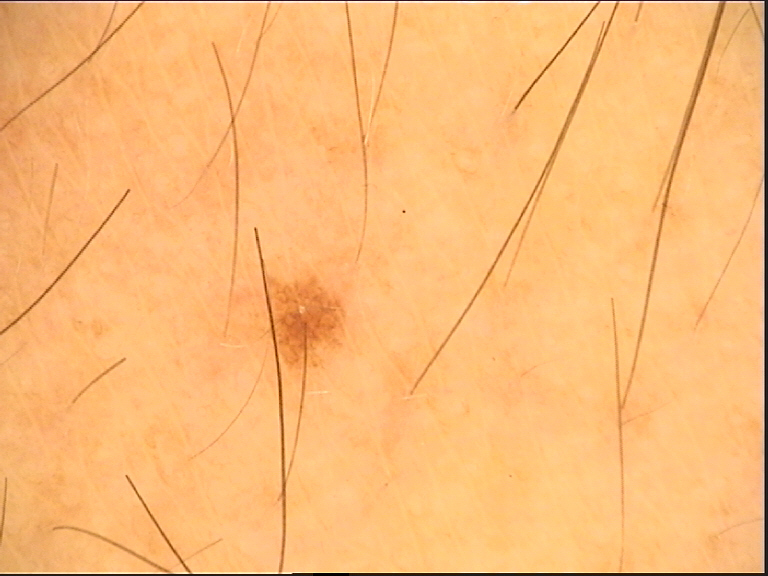Case:
A dermoscopic photograph of a skin lesion.
Conclusion:
The diagnostic label was a benign lesion — a dysplastic junctional nevus.